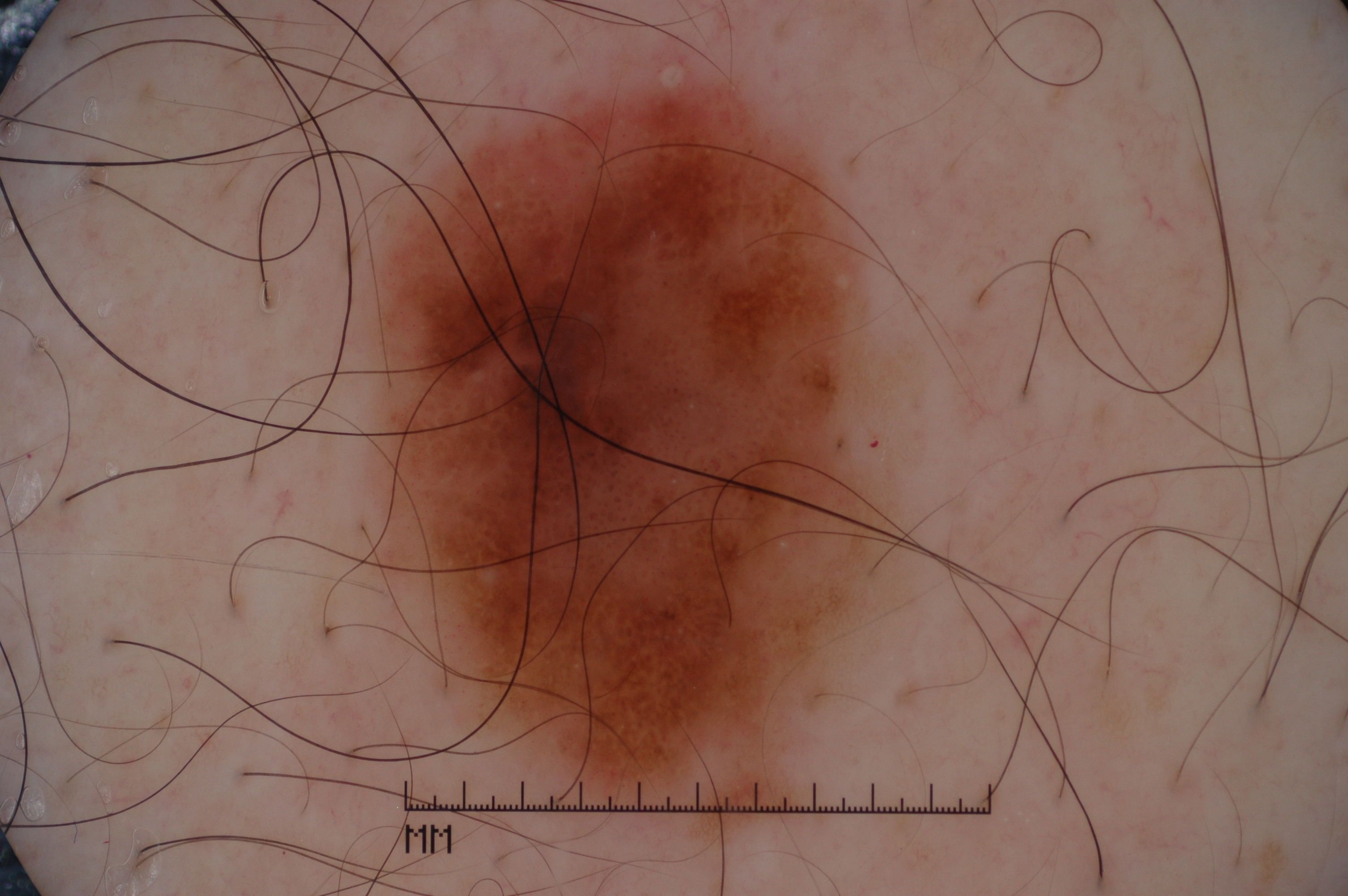Case summary: A male subject in their 70s. A dermoscopy image of a single skin lesion. With coordinates (x1, y1, x2, y2), the lesion's extent is <bbox>346, 50, 942, 814</bbox>. On dermoscopy, the lesion shows negative network, milia-like cysts, and pigment network. Pathology: The biopsy diagnosis was a melanoma, a malignant lesion.